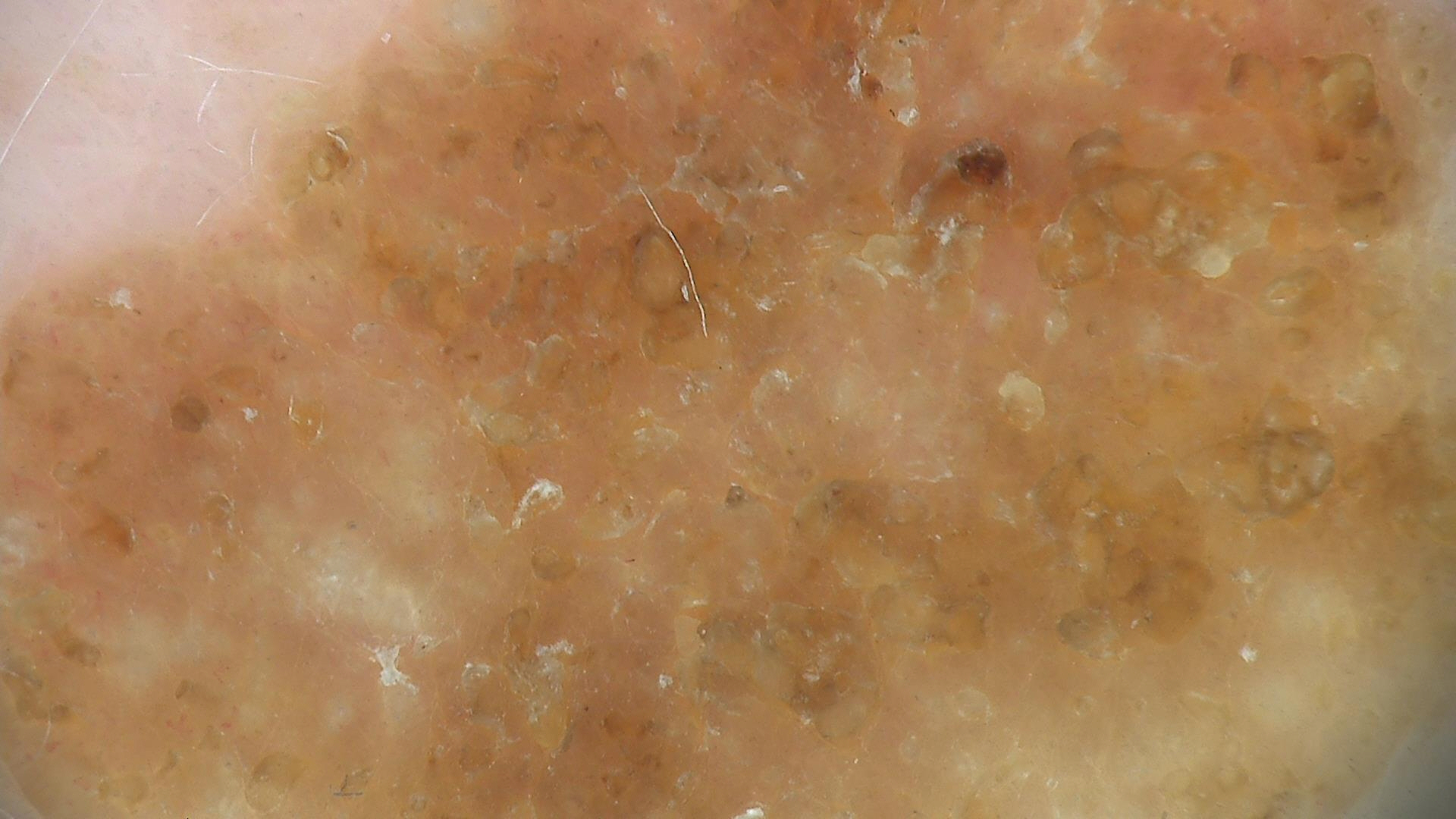imaging = dermatoscopy | subtype = keratinocytic | diagnosis = seborrheic keratosis (expert consensus).